A male patient about 75 years old; a skin lesion imaged with contact-polarized dermoscopy:
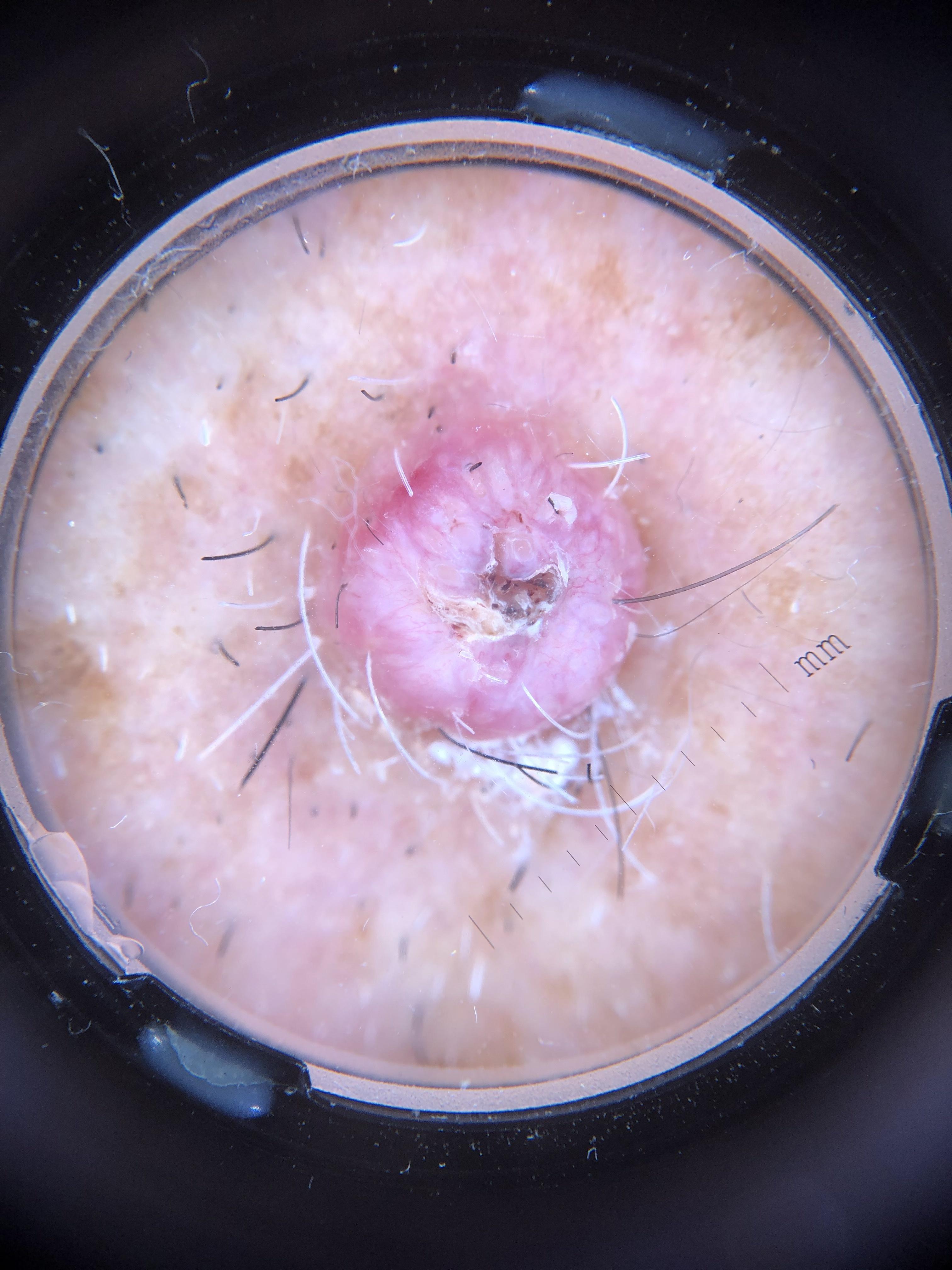location: the head or neck; diagnostic label: Squamous cell carcinoma (biopsy-proven).